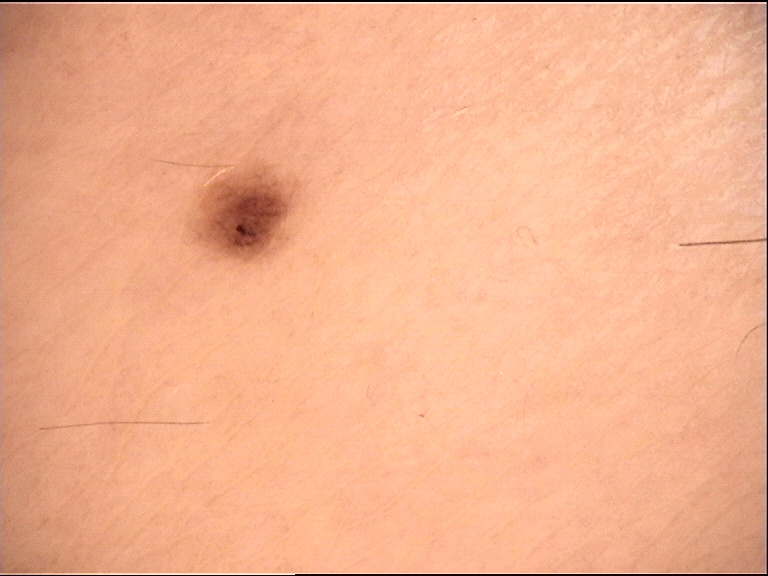Dermoscopy of a skin lesion. Consistent with a dysplastic junctional nevus.